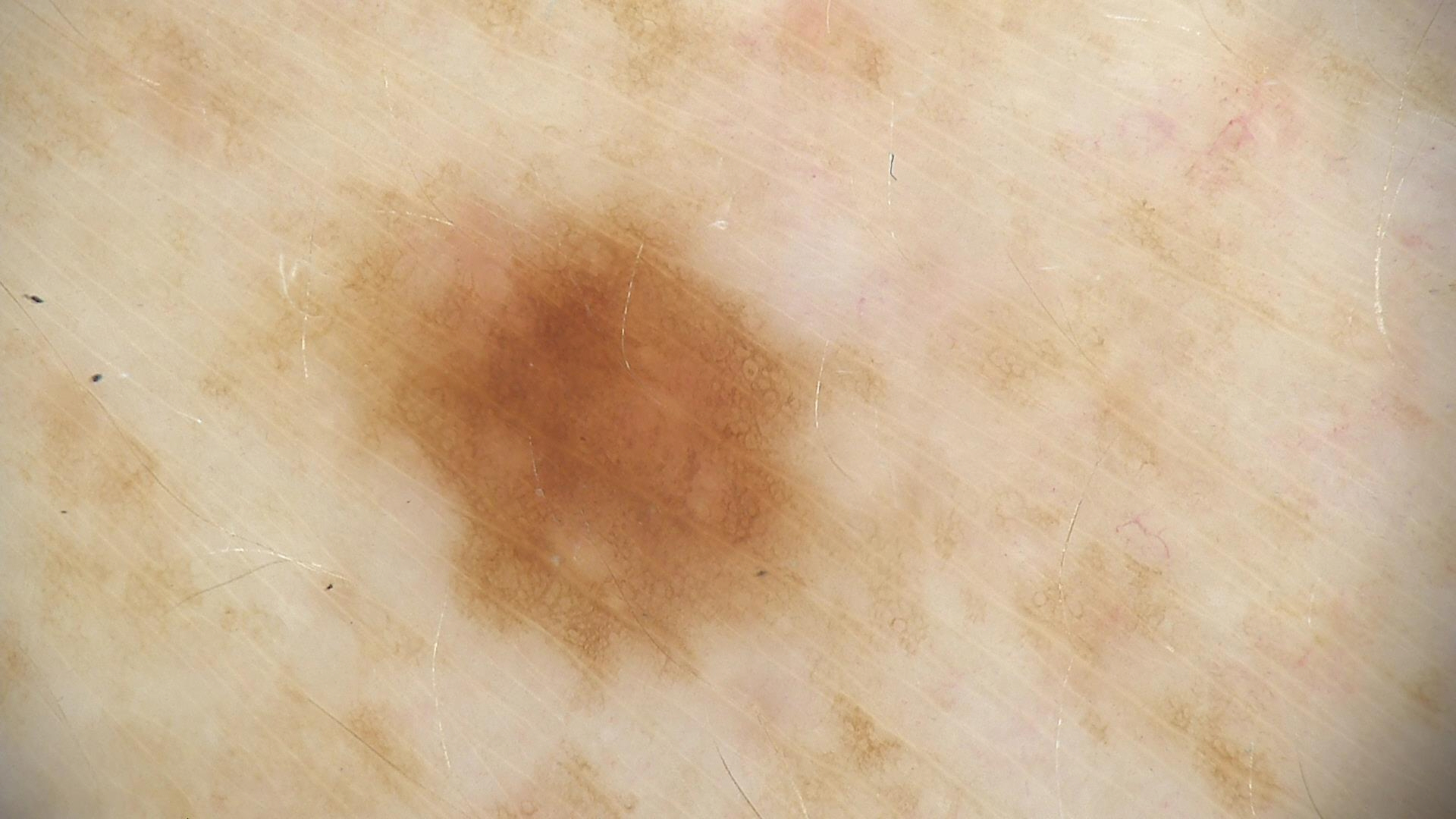Impression:
The diagnostic label was a dysplastic junctional nevus.